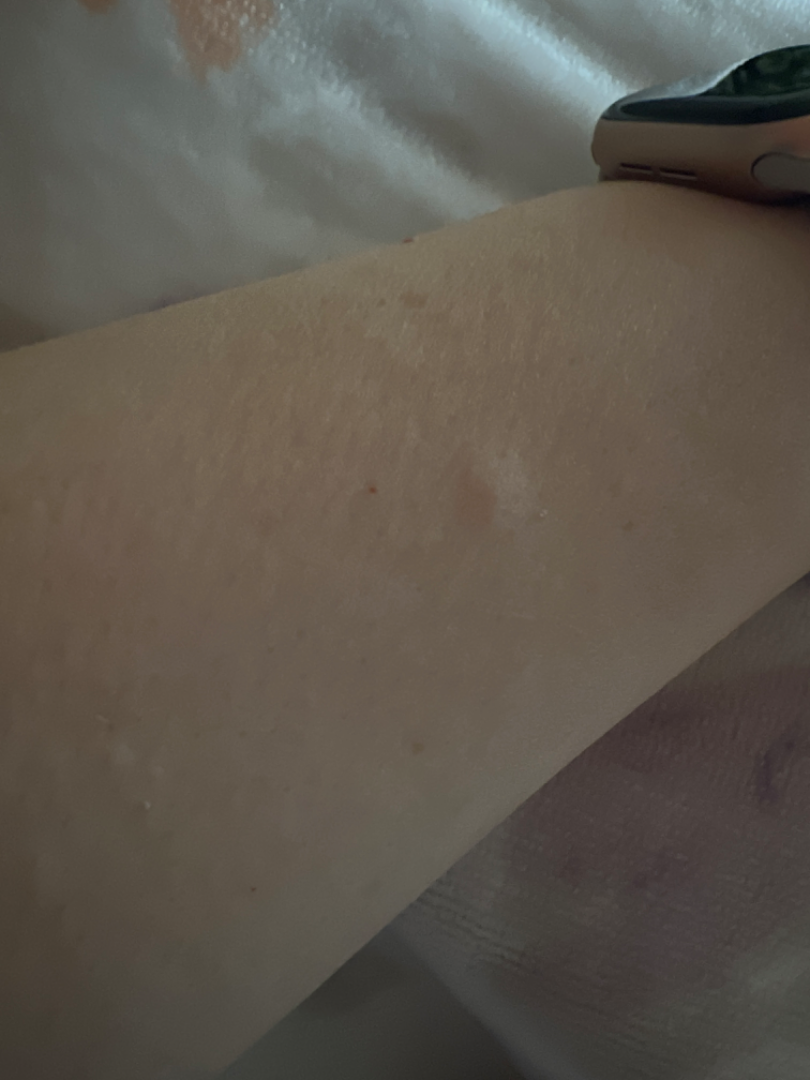Q: Anatomic location?
A: arm and leg
Q: How does the lesion feel?
A: raised or bumpy
Q: Image view?
A: close-up